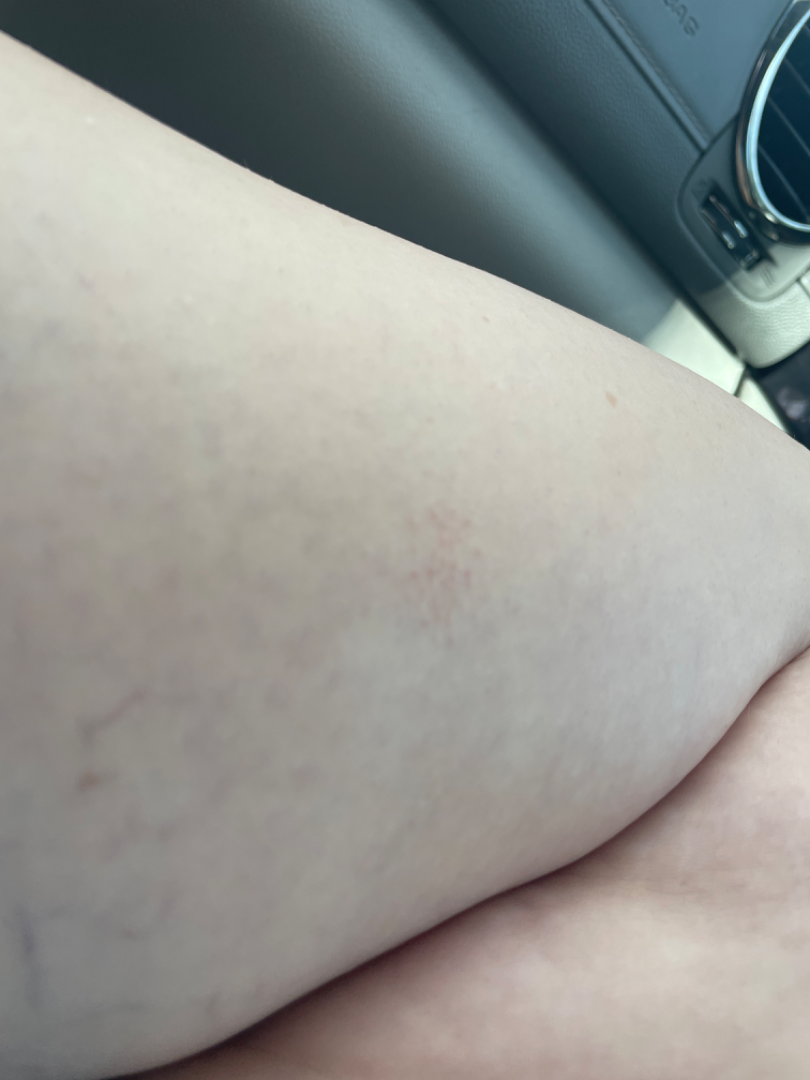The reviewing dermatologist's impression was: most consistent with Lichen spinulosus; an alternative is Eczema.